This image was taken at an angle, the patient is a female aged 18–29, the lesion involves the head or neck: 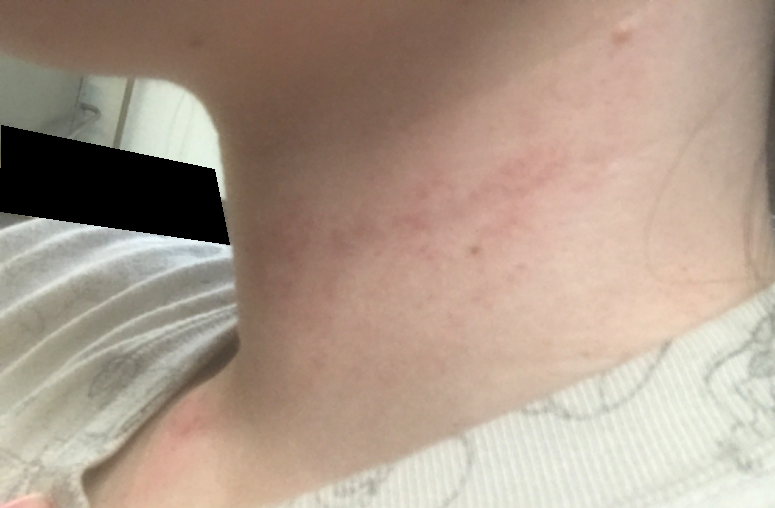{"texture": "flat", "duration": "about one day", "systemic_symptoms": "joint pain", "differential": {"Allergic Contact Dermatitis": 0.5, "Irritant Contact Dermatitis": 0.5}}